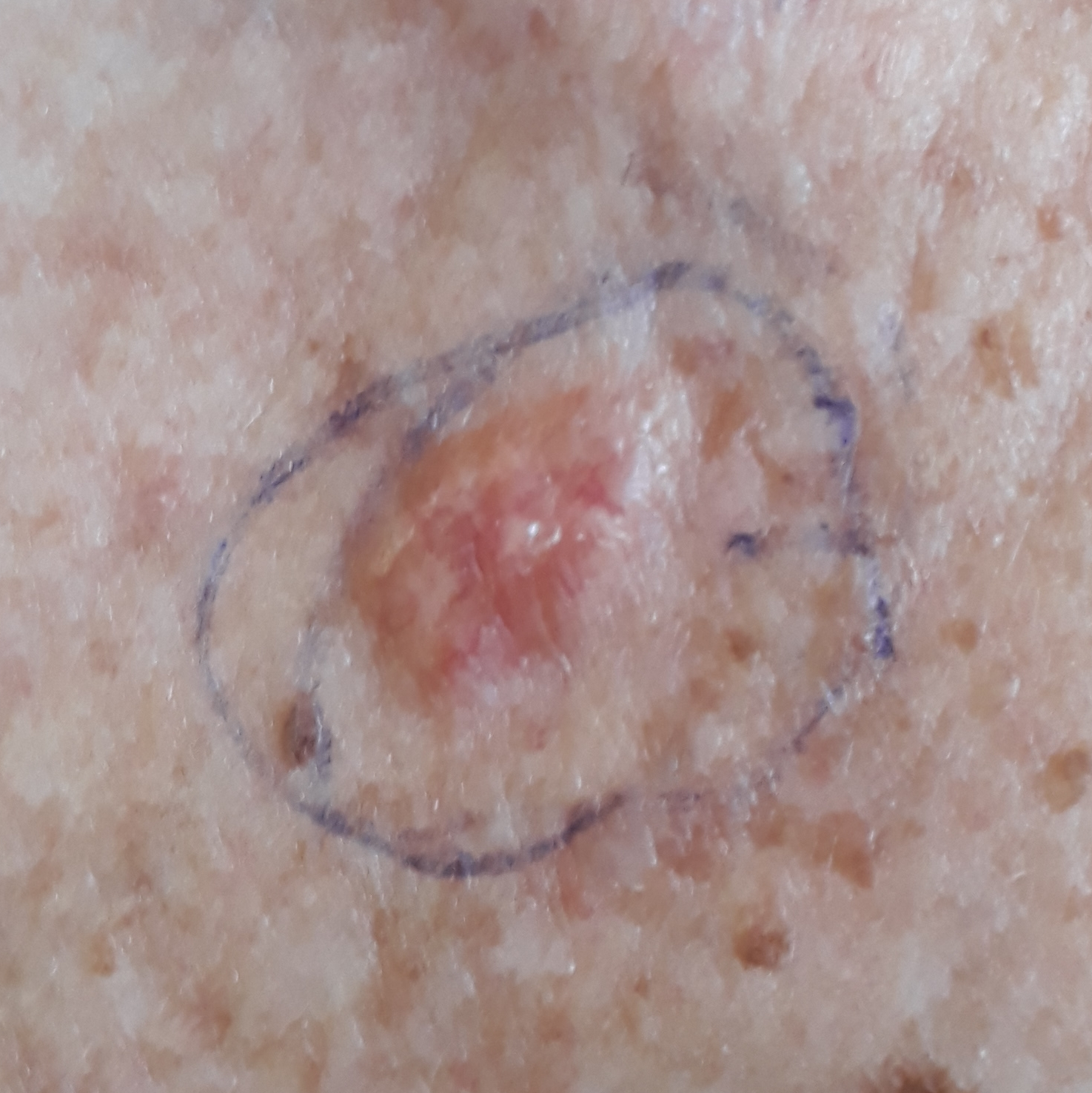The chart records prior malignancy (patient or family) and prior skin cancer (patient or family). The lesion involves the chest. The patient reports that the lesion is elevated and has bled. On biopsy, the diagnosis was a basal cell carcinoma.